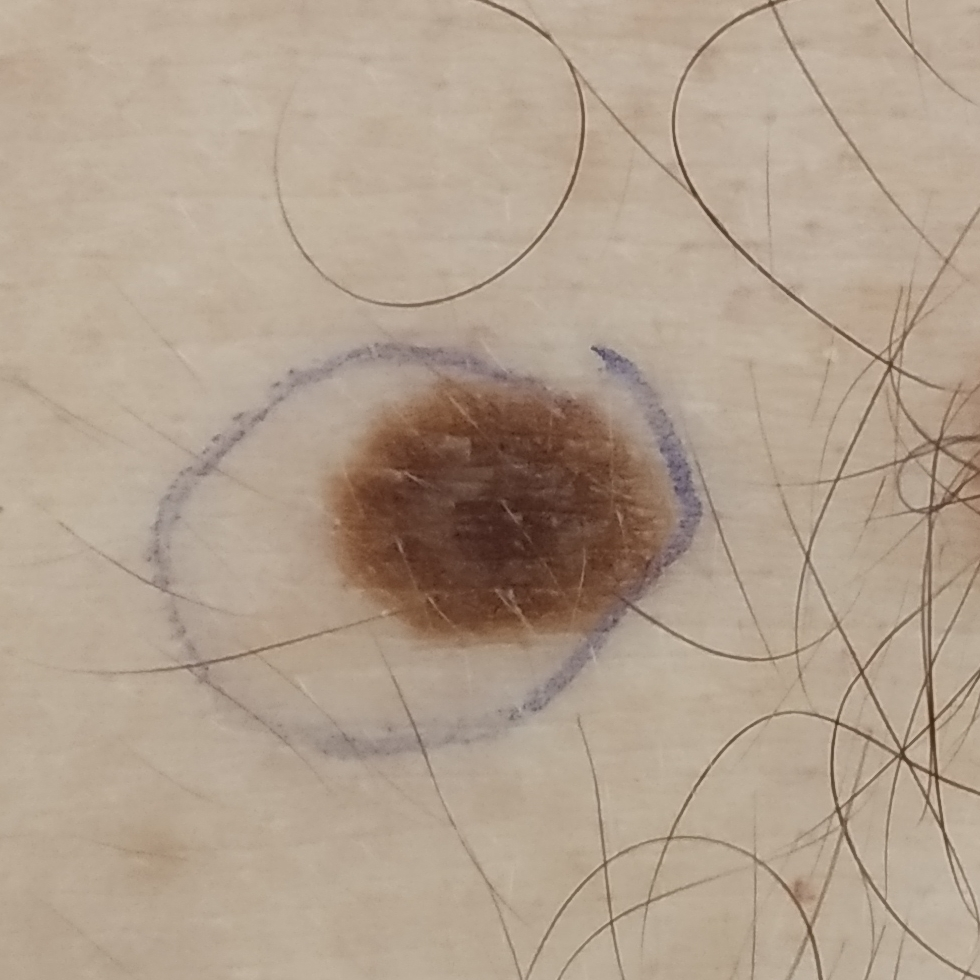The patient was assessed as Fitzpatrick skin type III.
A clinical photo of a skin lesion taken with a smartphone.
The lesion is on the abdomen.
Measuring about 15 × 12 mm.
The patient reports that the lesion has changed.
Clinically diagnosed as a benign lesion — a nevus.